A dermoscopic close-up of a skin lesion · the patient is skin type IV · a female patient aged 53-57.
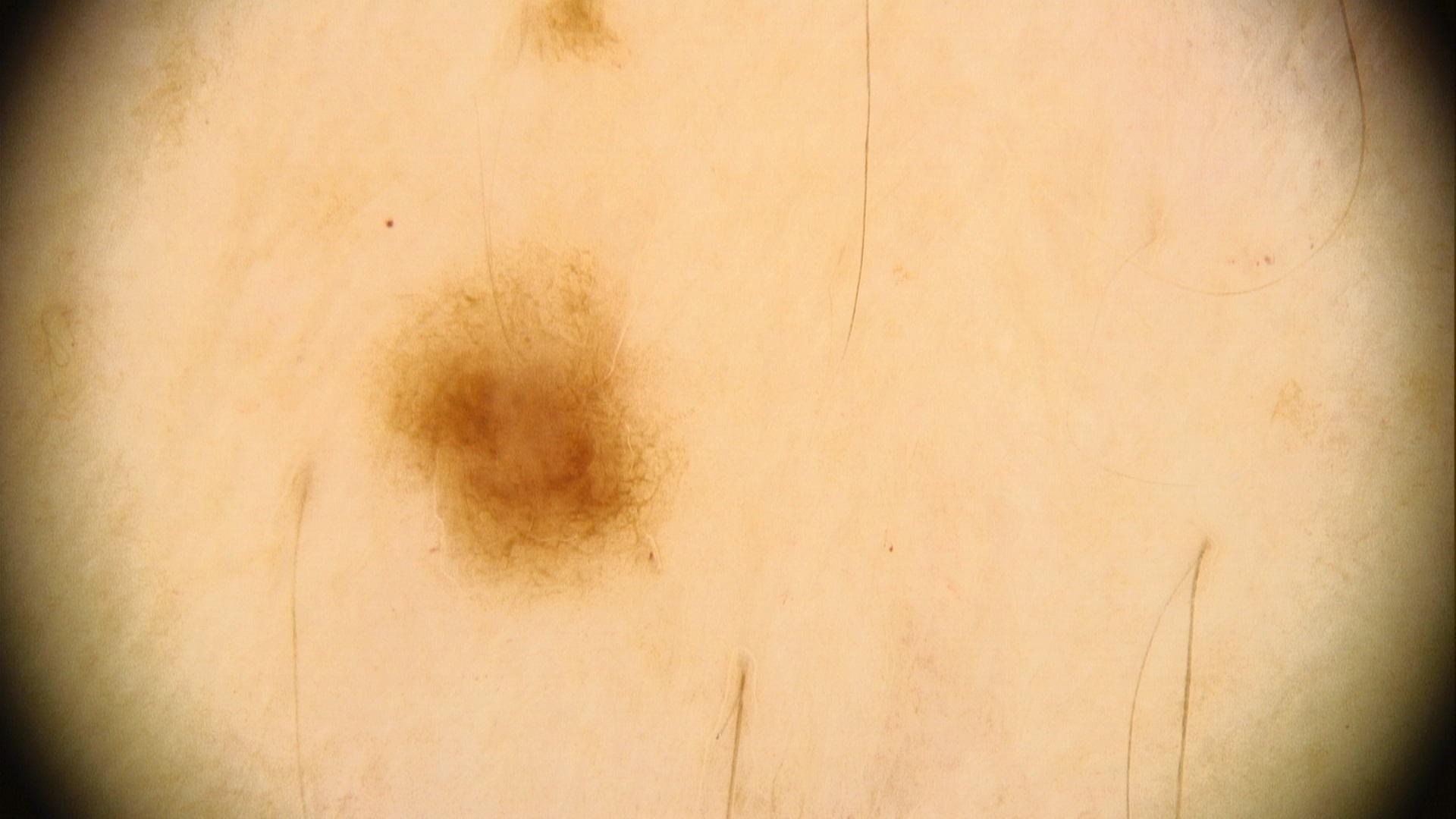Q: What is the diagnosis?
A: Nevus